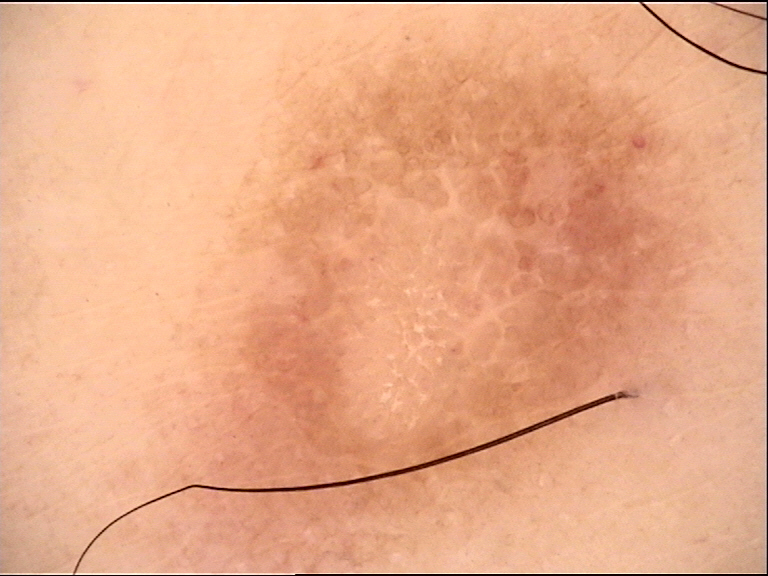lesion_type:
  main_class: fibro-histiocytic
diagnosis:
  name: dermatofibroma
  code: df
  malignancy: benign
  super_class: non-melanocytic
  confirmation: expert consensus